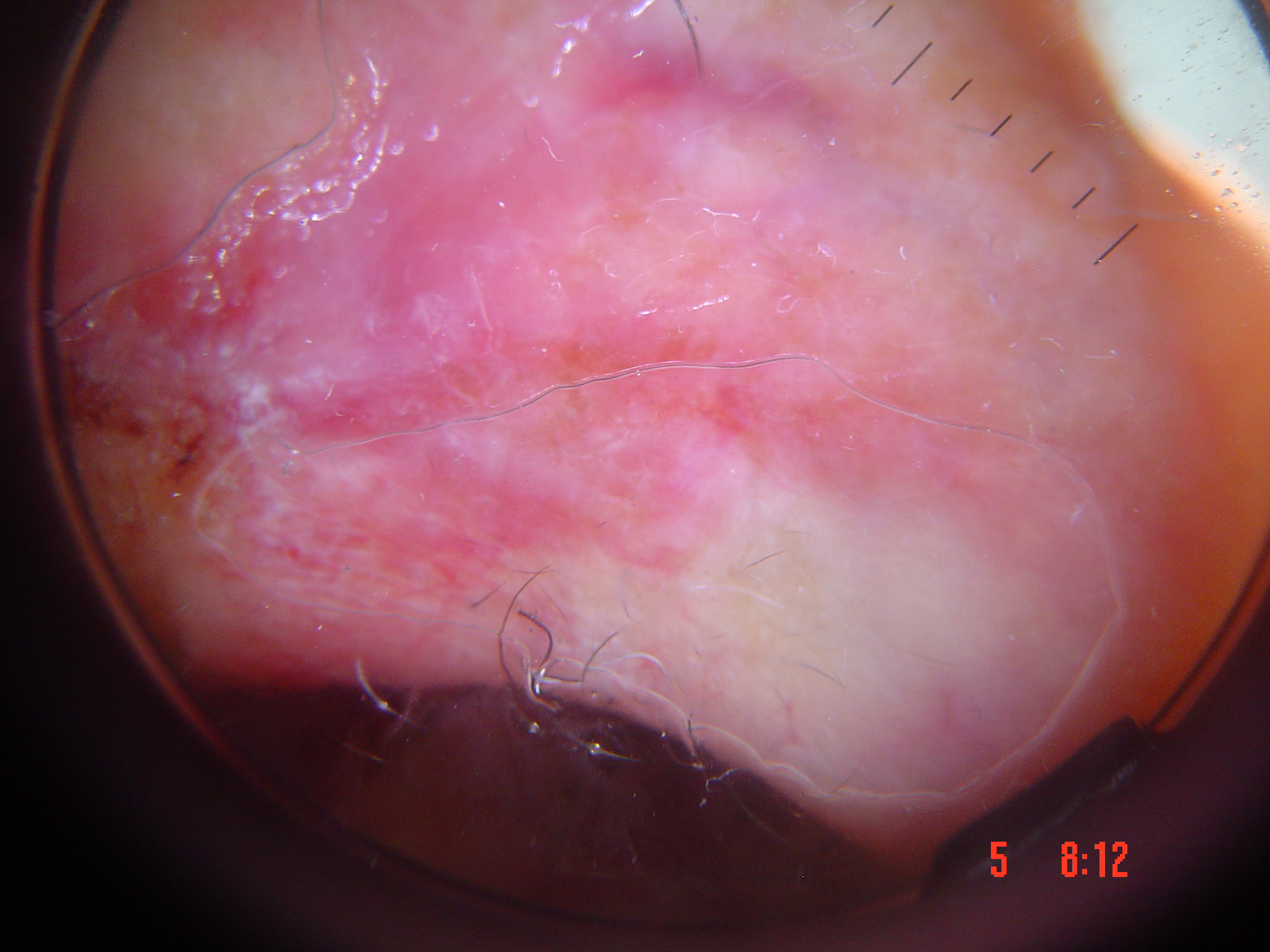{
  "image": "dermatoscopy",
  "diagnosis": {
    "name": "basal cell carcinoma",
    "code": "bcc",
    "malignancy": "malignant",
    "super_class": "non-melanocytic",
    "confirmation": "histopathology"
  }
}